The subject is 40–49, male. Located on the arm and leg. This is a close-up image — 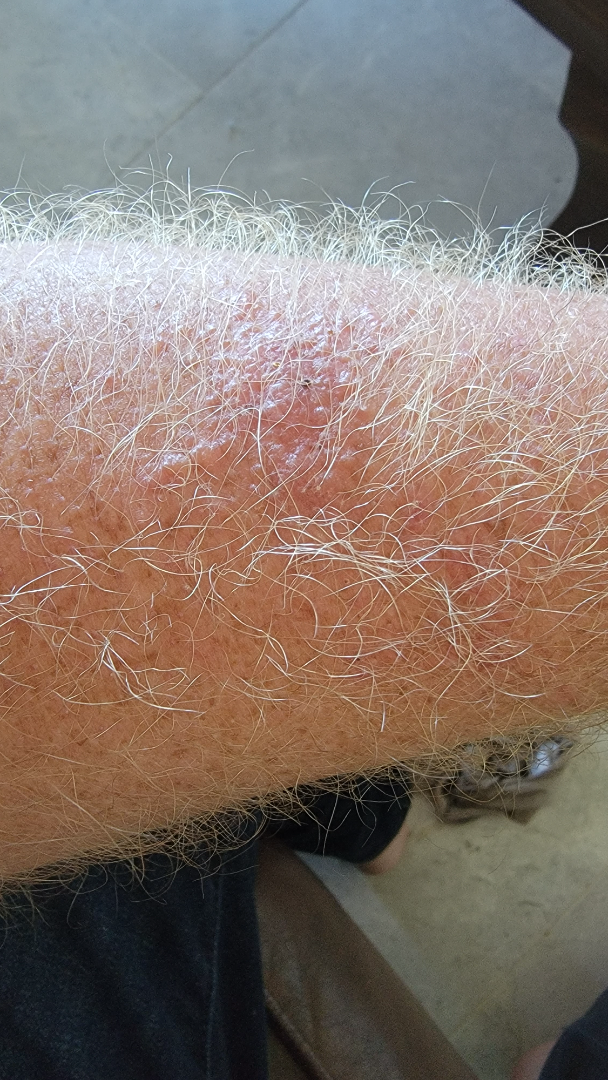assessment: could not be assessed